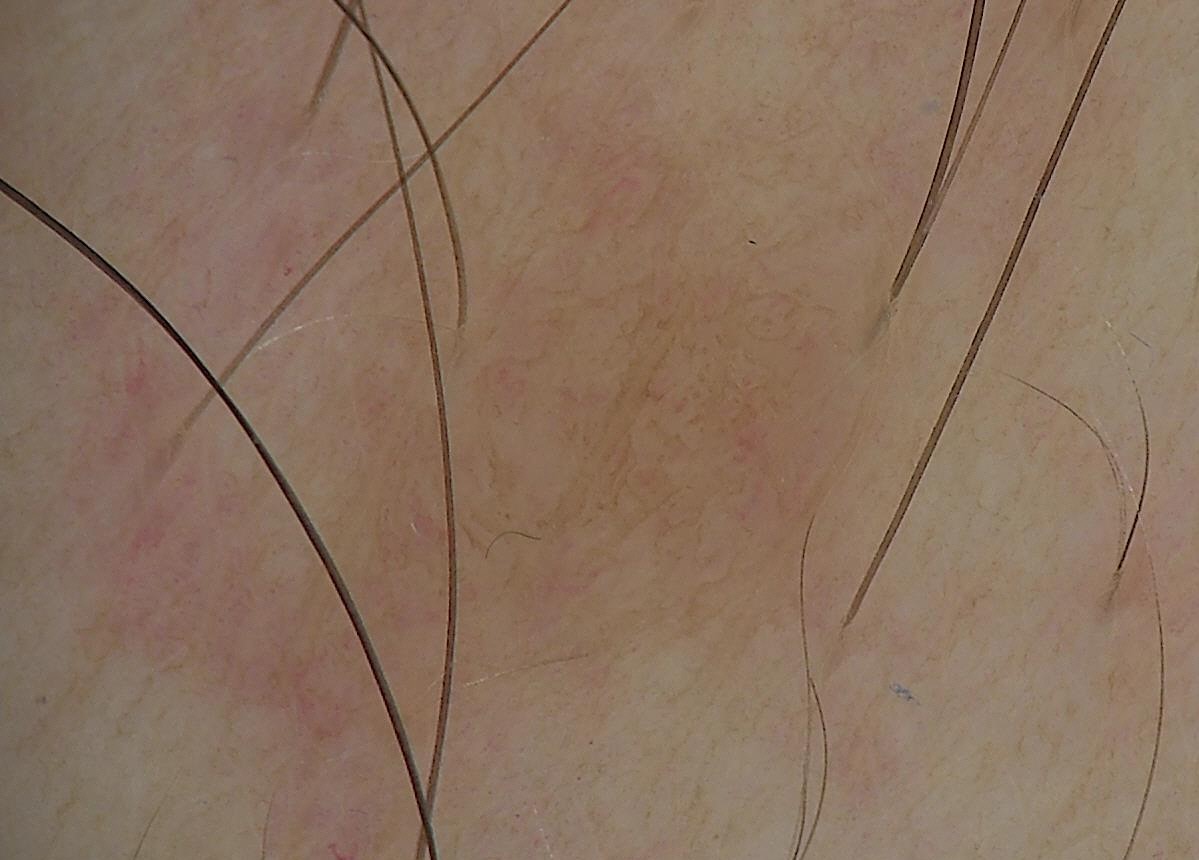Findings:
A skin lesion imaged with a dermatoscope. The architecture is that of a banal lesion.
Impression:
Consistent with a dermal nevus.